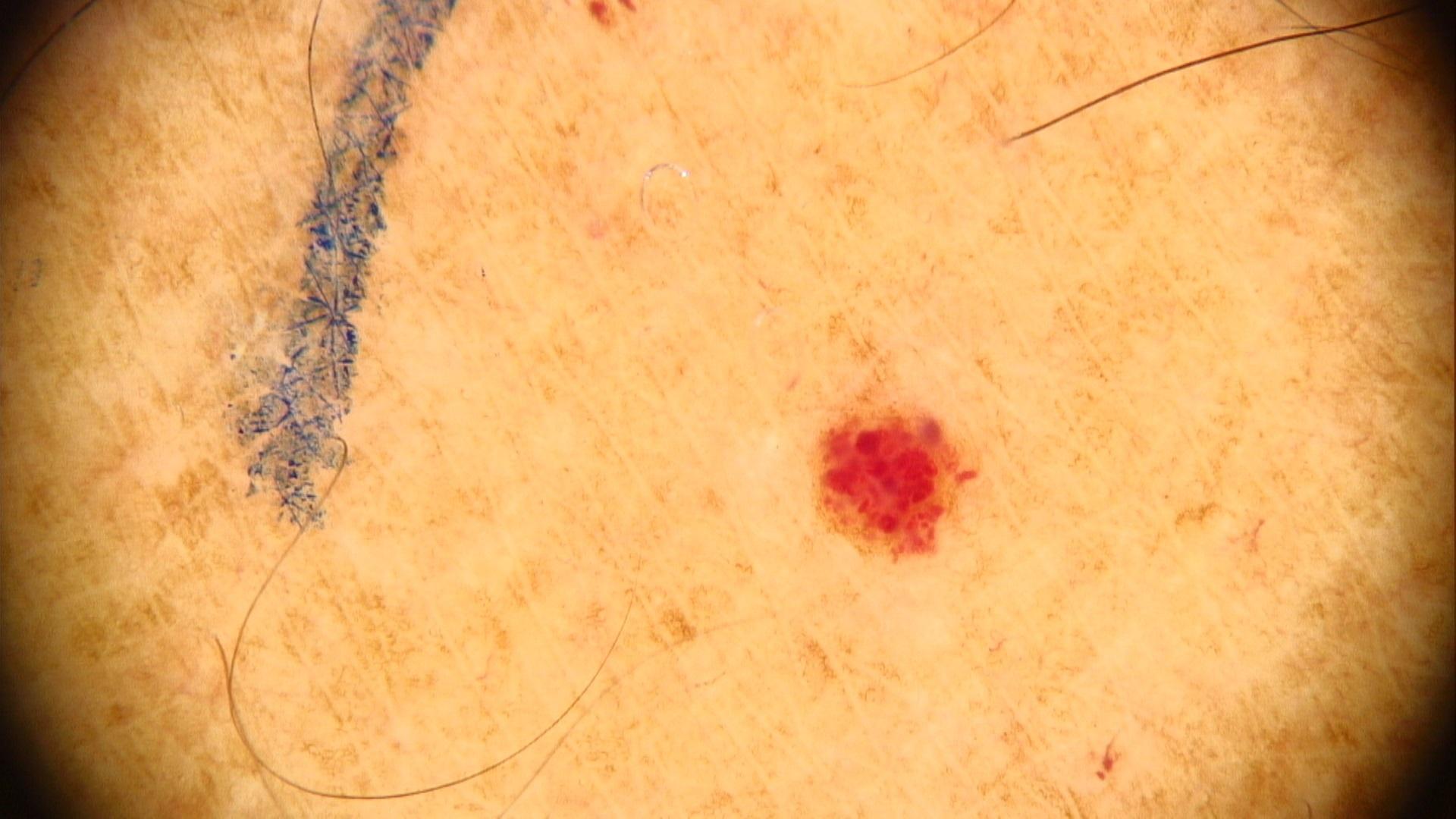Contact-polarized dermoscopy of a skin lesion. A male subject approximately 65 years of age. The lesion is on an upper extremity. Expert review favored a vascular lesion.